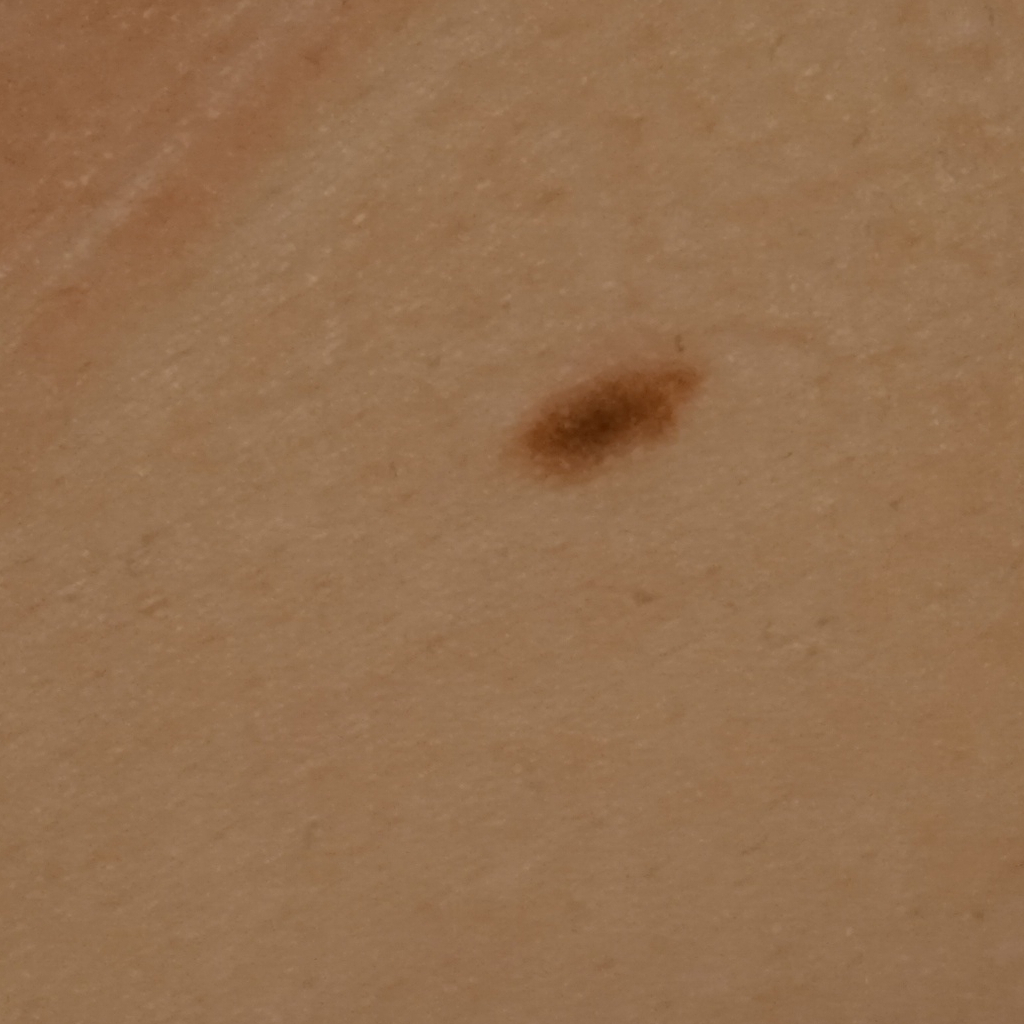Findings:
- diagnostic label: melanocytic nevus (dermatologist consensus)